A female subject aged 81. Acquired for a research image collection, with no referral diagnosis. On a questionnaire the patient reported no personal history of skin cancer and no sunbed use. The patient says their skin reddens painfully with sun exposure. A skin lesion imaged with a dermatoscope: 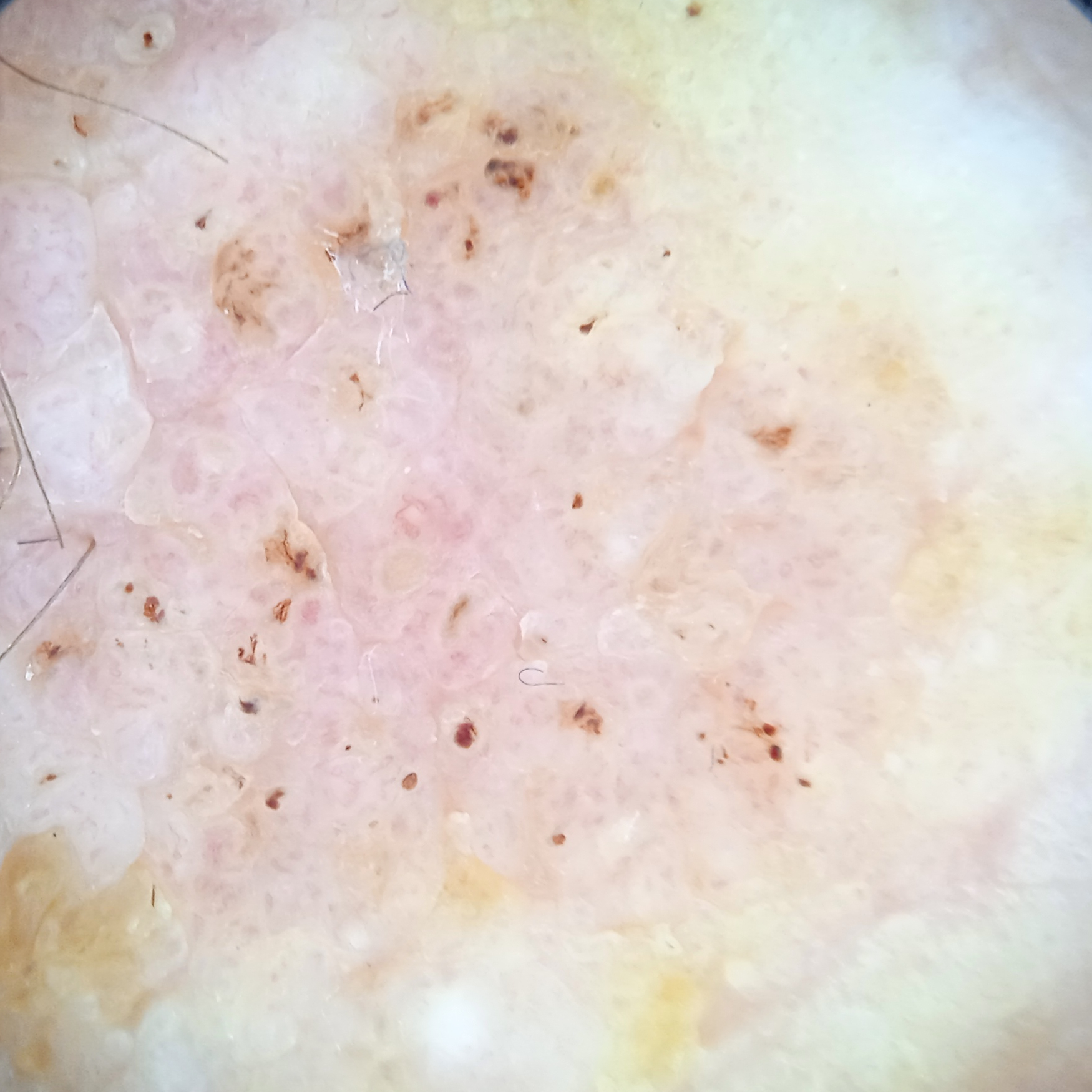Findings: The lesion is located on the face. The lesion is about 36.6 mm across. Conclusion: The diagnostic impression was a seborrheic keratosis.